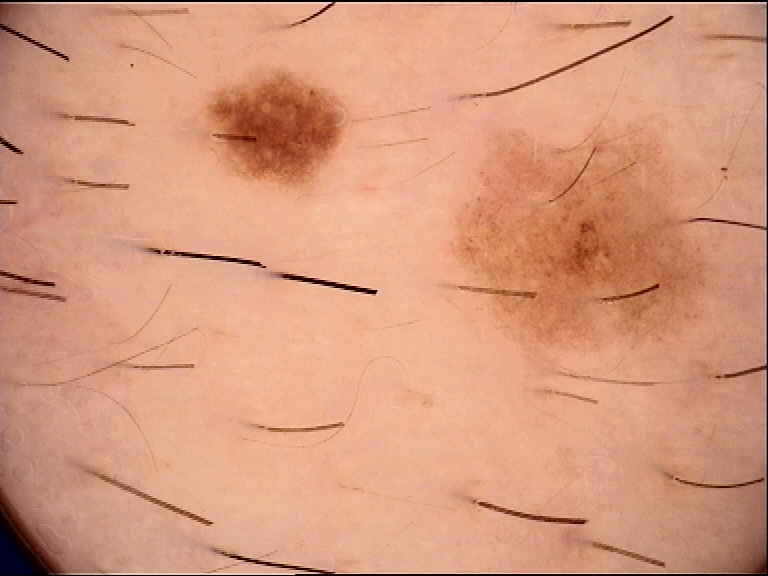Case: A dermoscopic close-up of a skin lesion. Conclusion: Labeled as a dysplastic junctional nevus.